A skin lesion imaged with a dermatoscope.
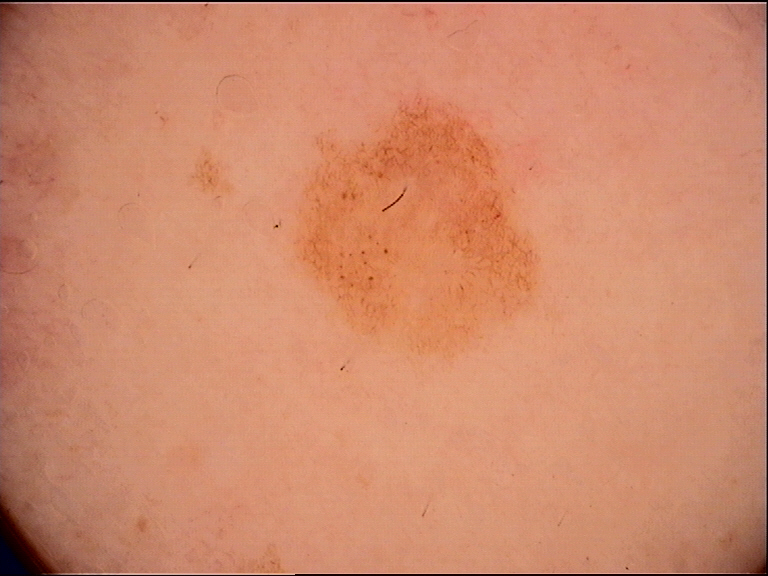Classified as a dysplastic junctional nevus.